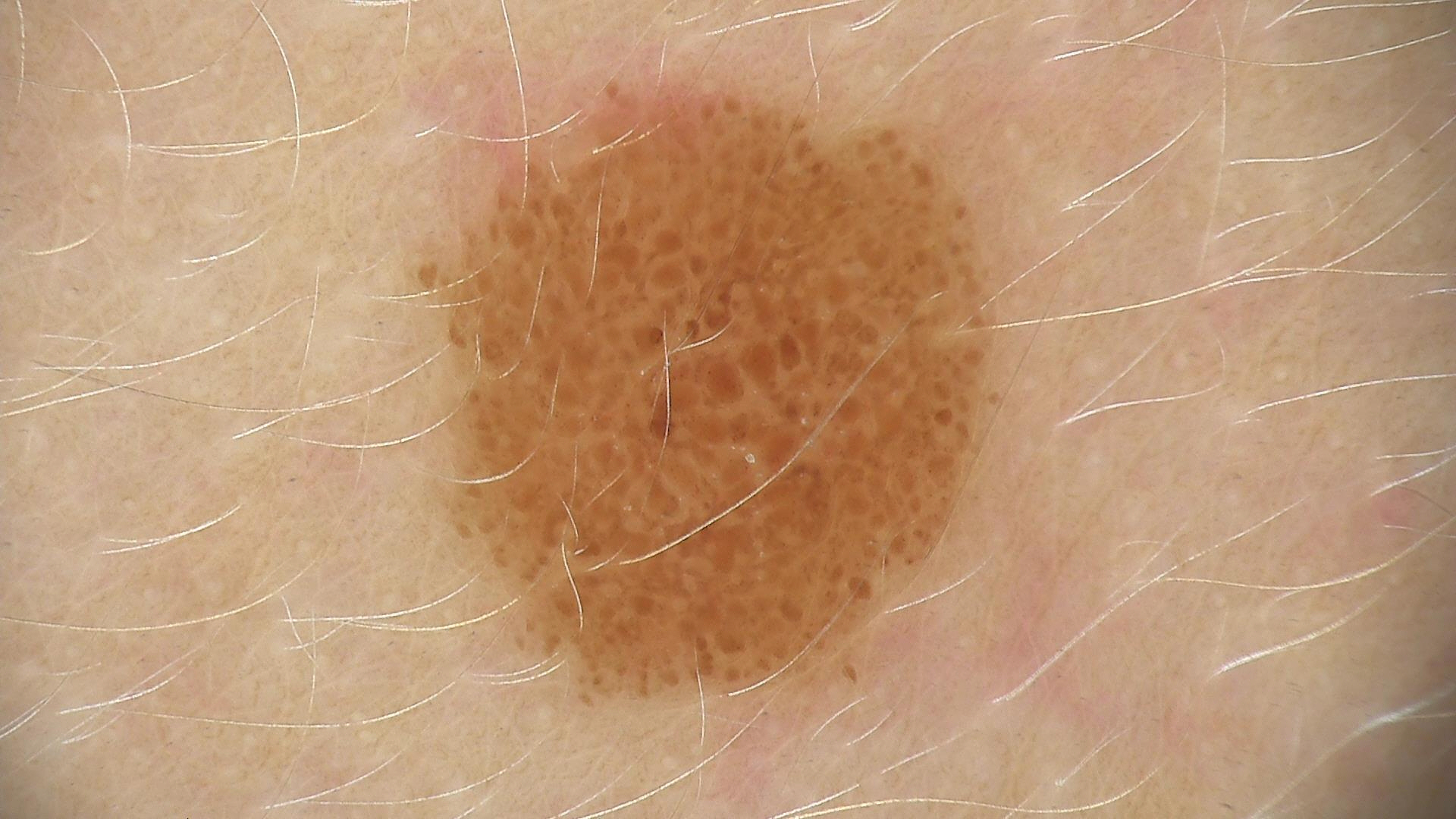modality = dermatoscopy
assessment = dysplastic compound nevus (expert consensus)